The photo was captured at an angle. Female patient, age 18–29. The back of the hand and palm are involved — 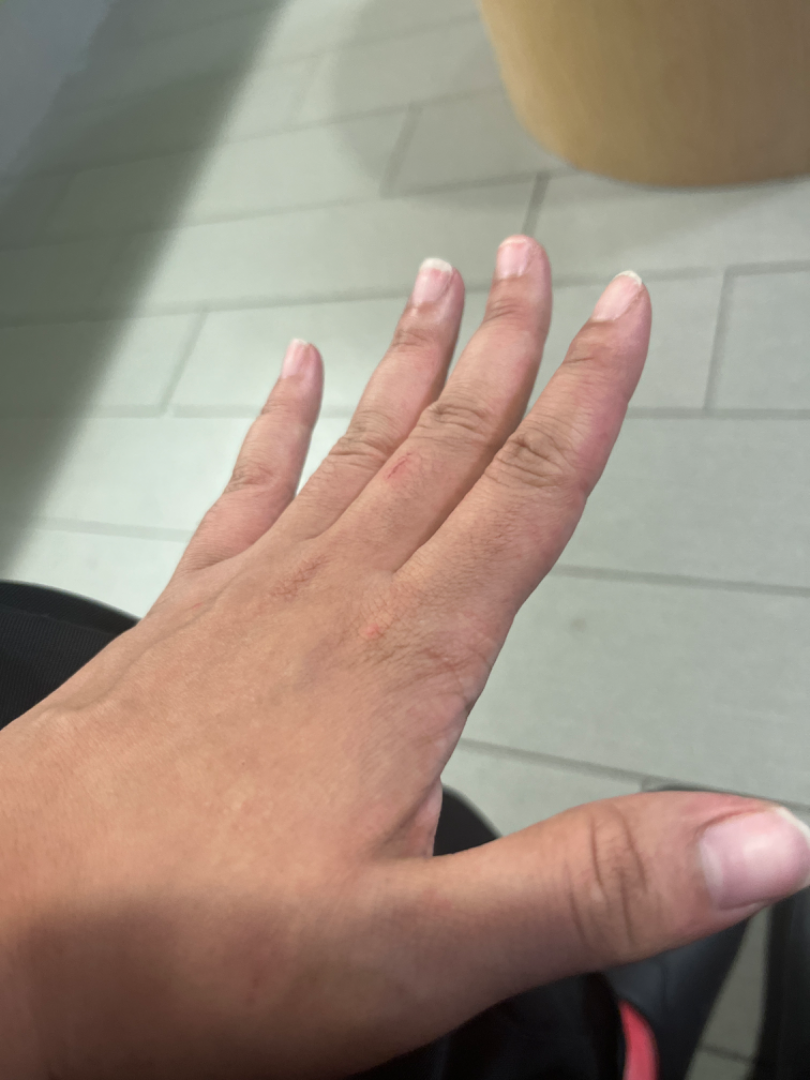dermatologist impression: most likely Eczema; the differential also includes Chilblain